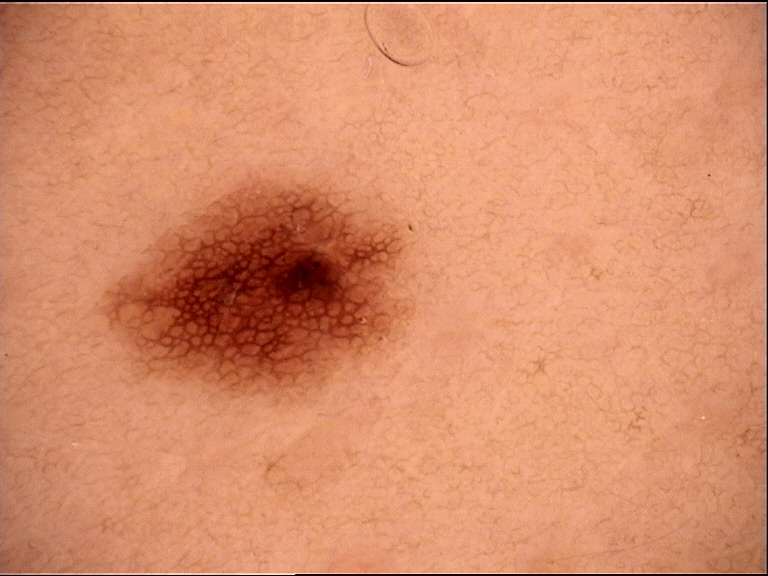Summary:
A dermoscopy image of a single skin lesion.
Impression:
Diagnosed as a benign lesion — a dysplastic junctional nevus.